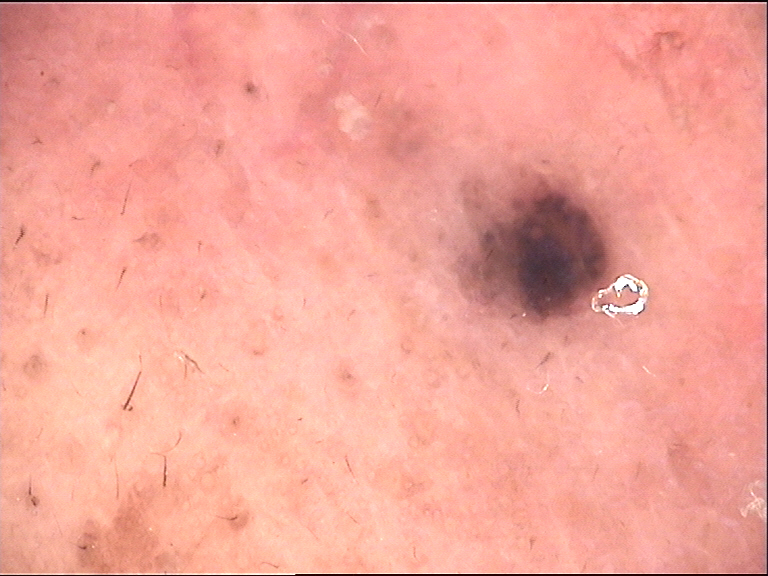A dermoscopic close-up of a skin lesion. Labeled as a dermal lesion — a blue nevus.